A dermoscopic close-up of a skin lesion:
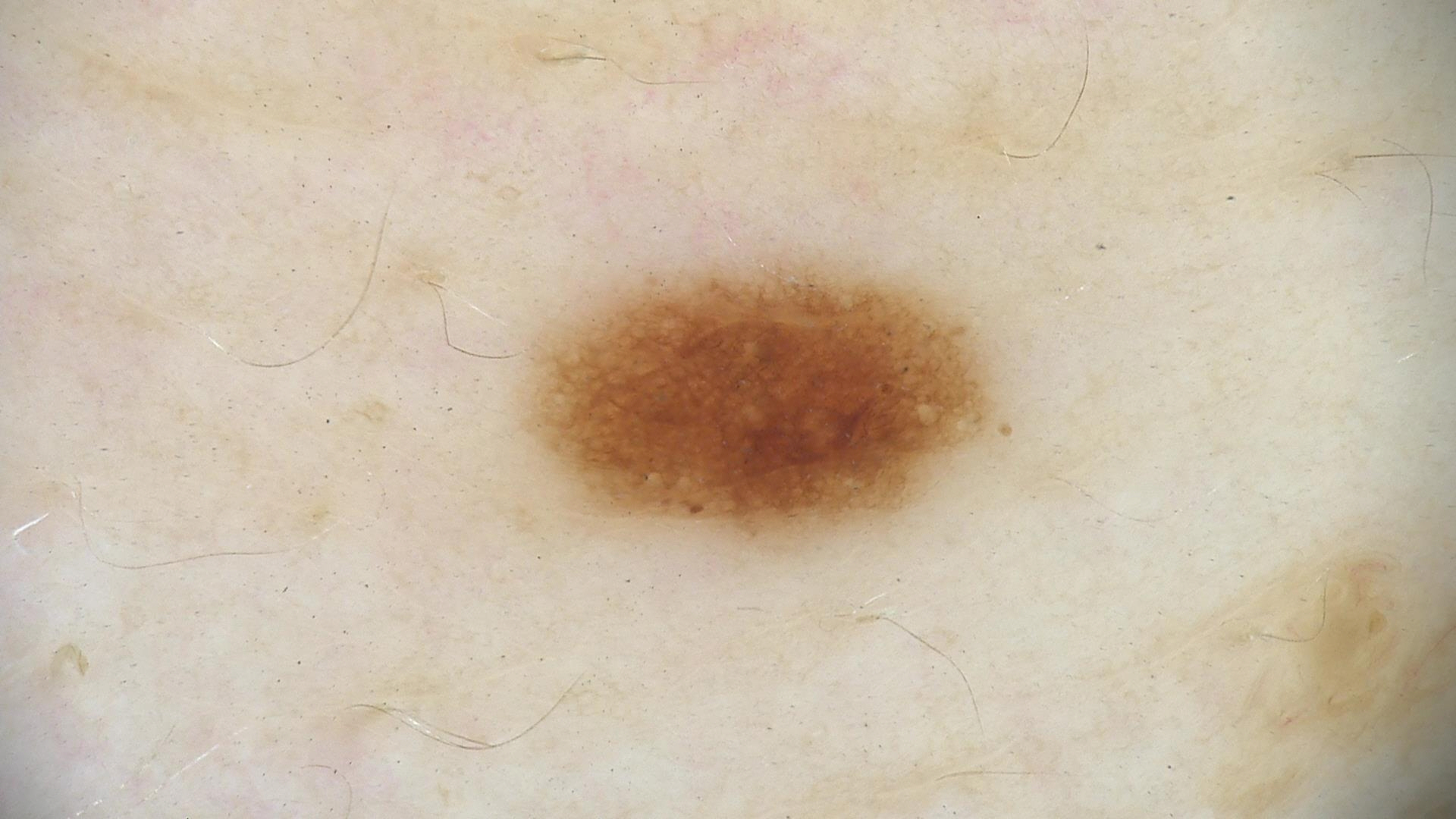diagnostic label=dysplastic junctional nevus (expert consensus).